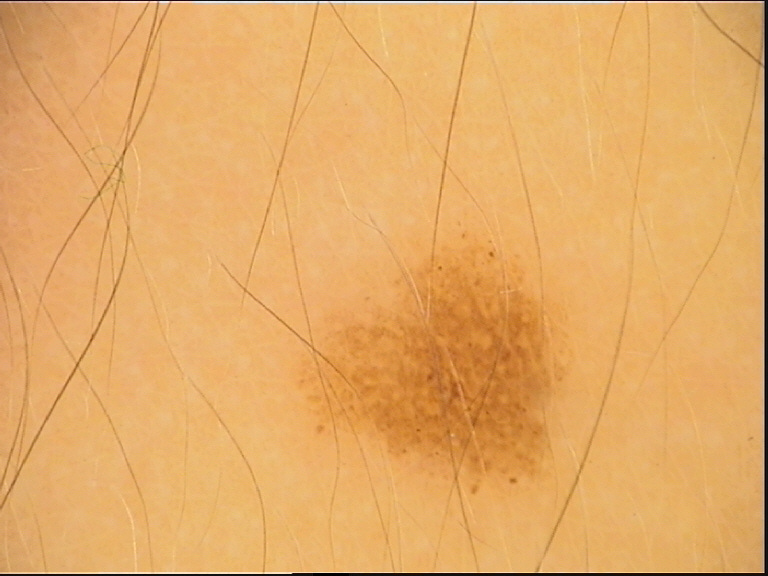- diagnostic label — dysplastic junctional nevus (expert consensus)